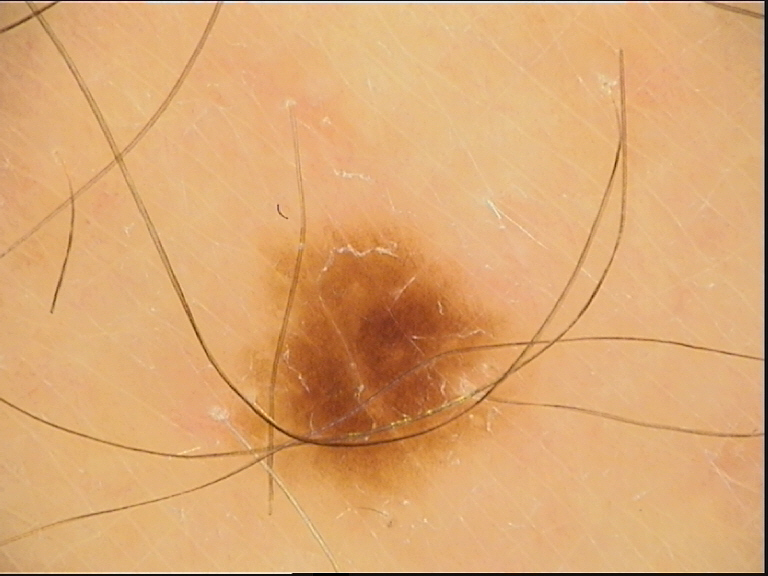A dermoscopic photograph of a skin lesion. The diagnosis was a dysplastic junctional nevus.